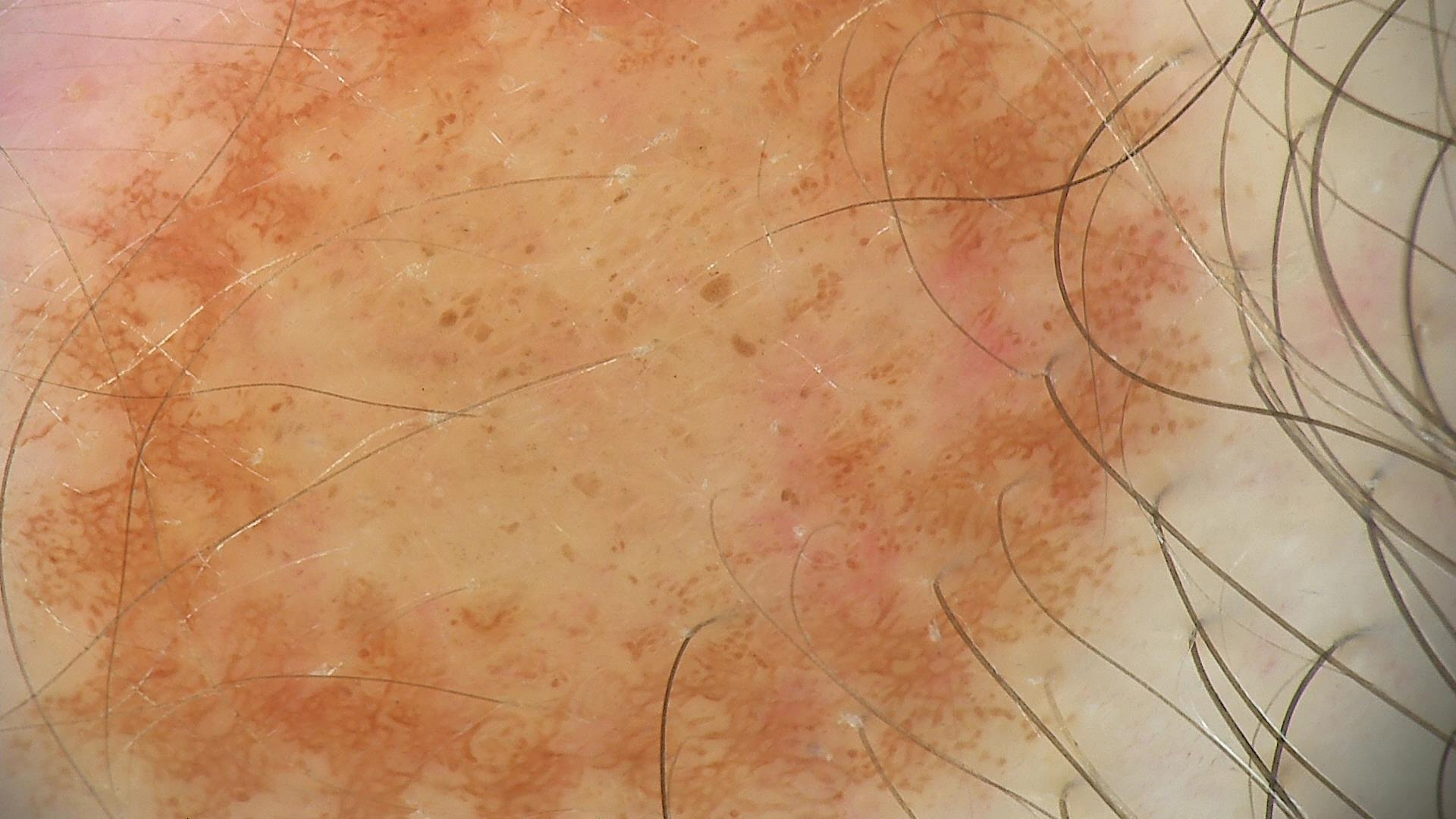| feature | finding |
|---|---|
| diagnosis | dysplastic junctional nevus (expert consensus) |